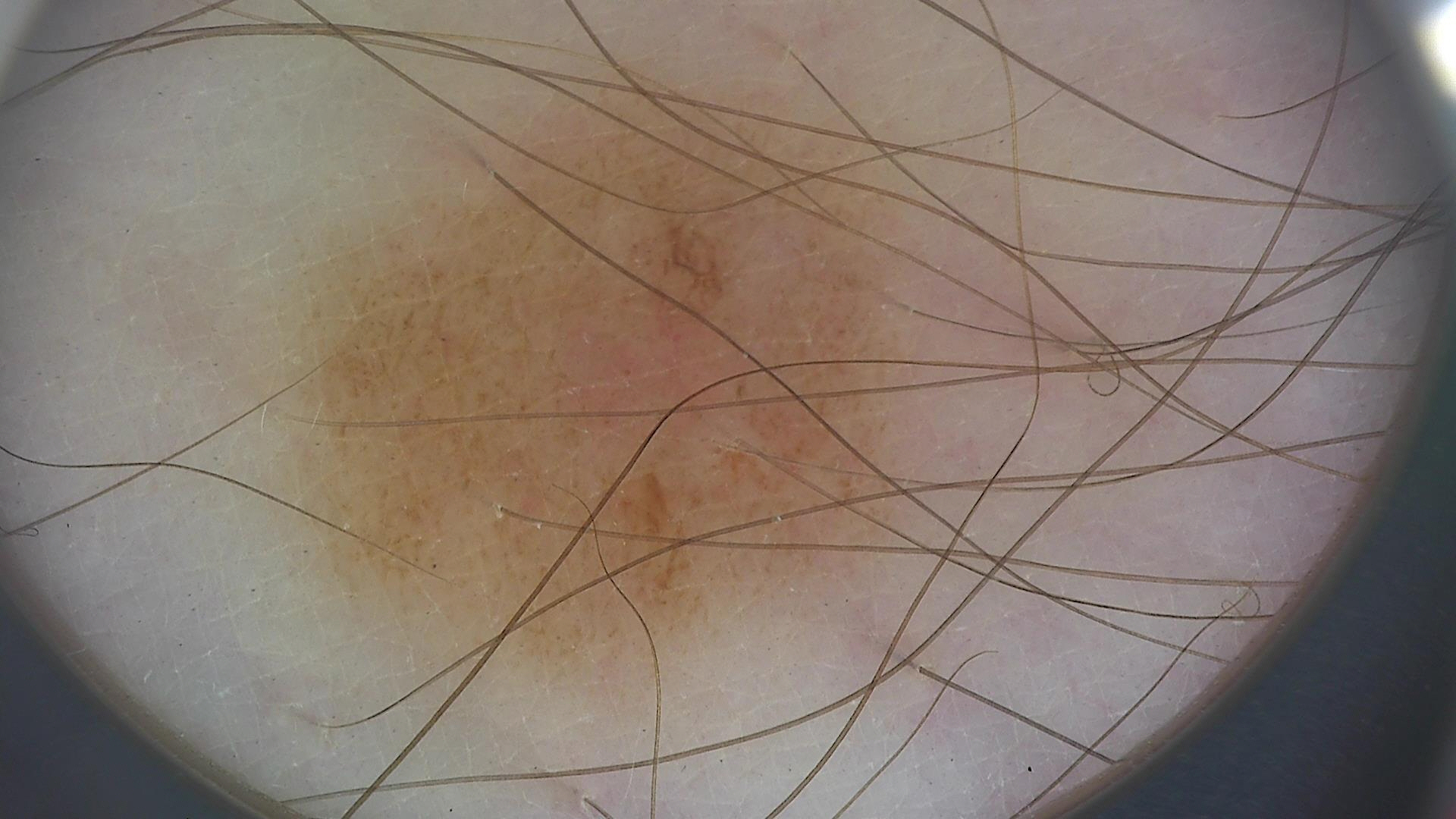{
  "image": "dermoscopy",
  "diagnosis": {
    "name": "dysplastic junctional nevus",
    "code": "jd",
    "malignancy": "benign",
    "super_class": "melanocytic",
    "confirmation": "expert consensus"
  }
}